A dermatoscopic image of a skin lesion:
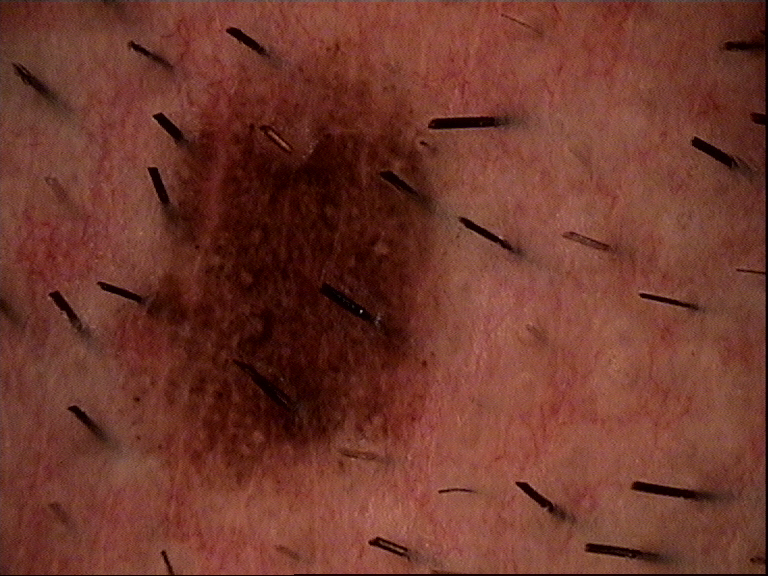Impression:
The diagnostic label was a benign lesion — a dysplastic compound nevus.